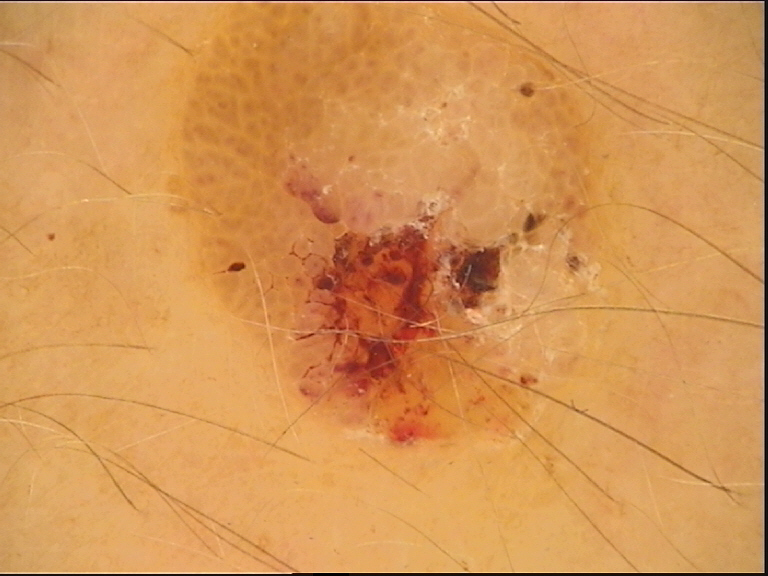– imaging: dermoscopy
– diagnostic label: seborrheic keratosis (expert consensus)